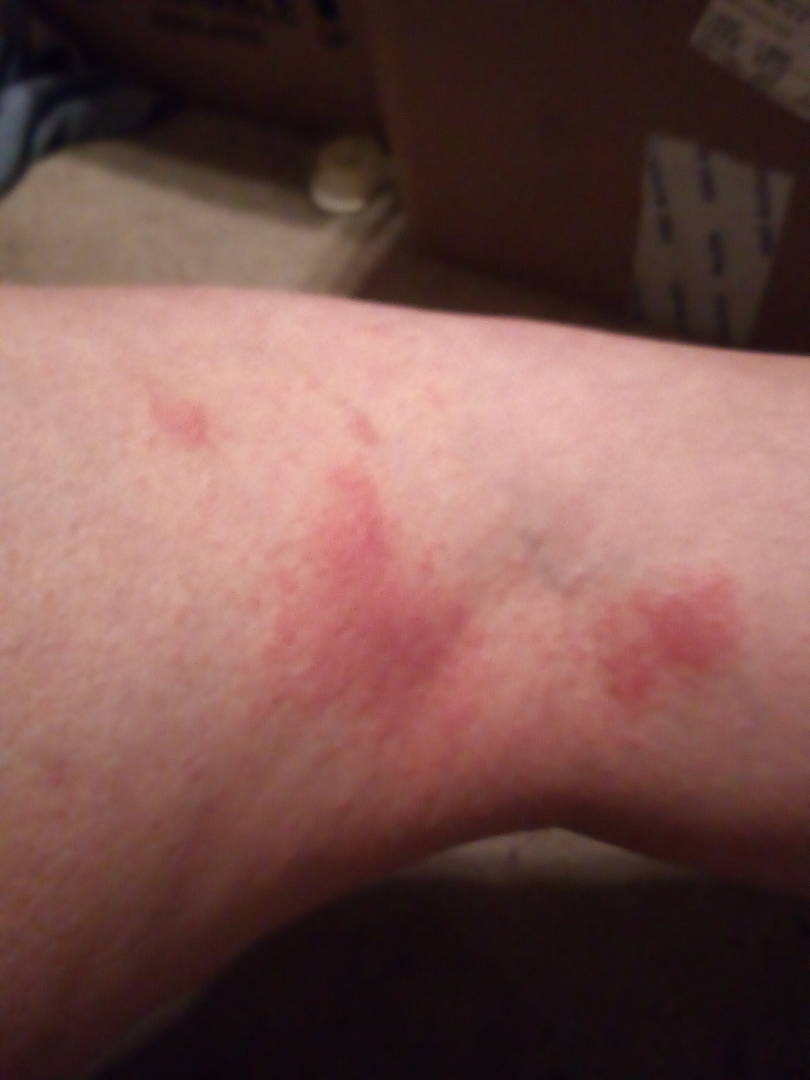Clinical context:
This image was taken at an angle. Fitzpatrick phototype II; lay graders estimated Monk Skin Tone 3–4.
Assessment:
On dermatologist assessment of the image, most consistent with Eczema; the differential also includes Allergic Contact Dermatitis.